A male patient aged 79; a skin lesion imaged with a dermatoscope; acquired for a research image collection, with no referral diagnosis.
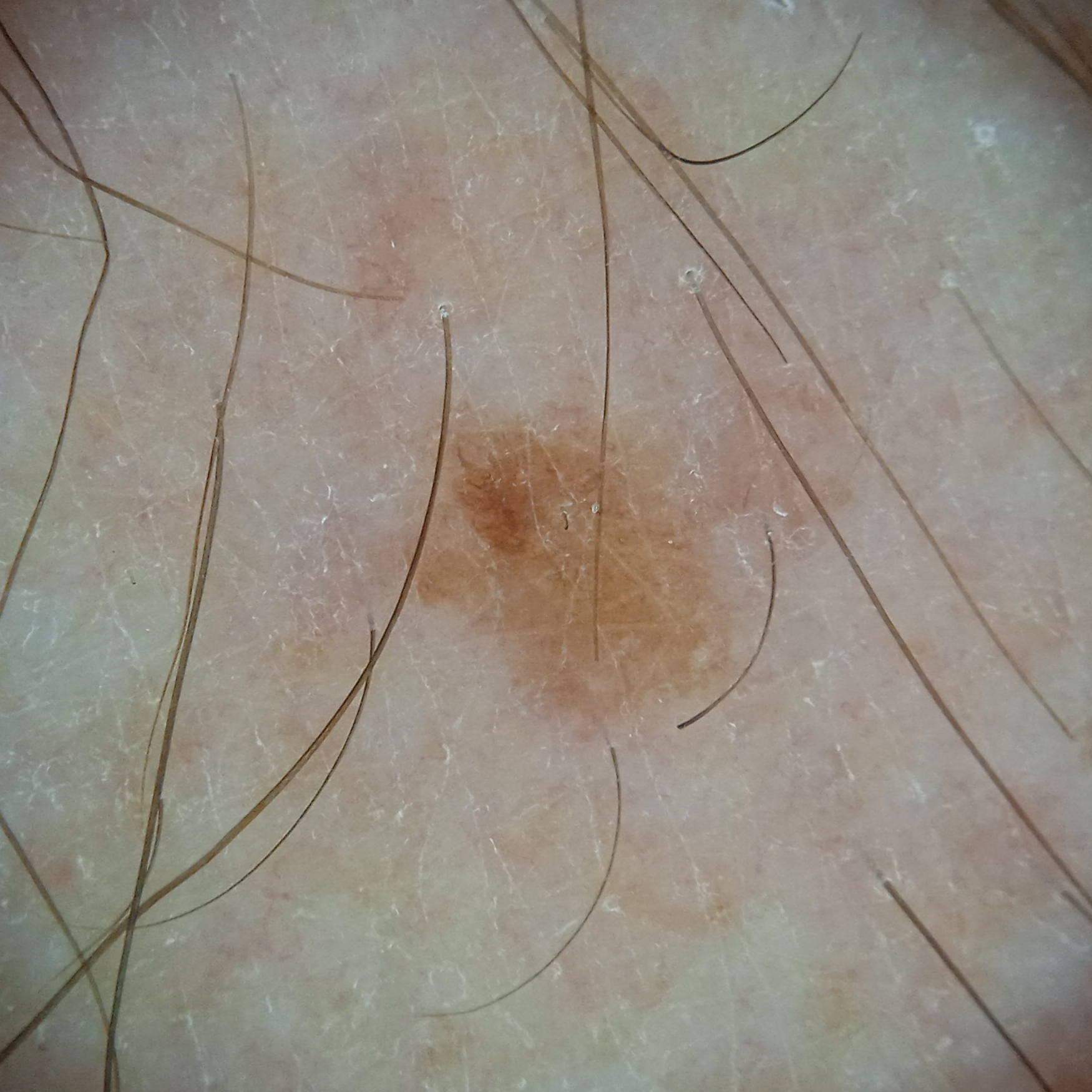Located on an arm. The lesion is about 4.2 mm across. The consensus diagnosis for this lesion was a seborrheic keratosis.